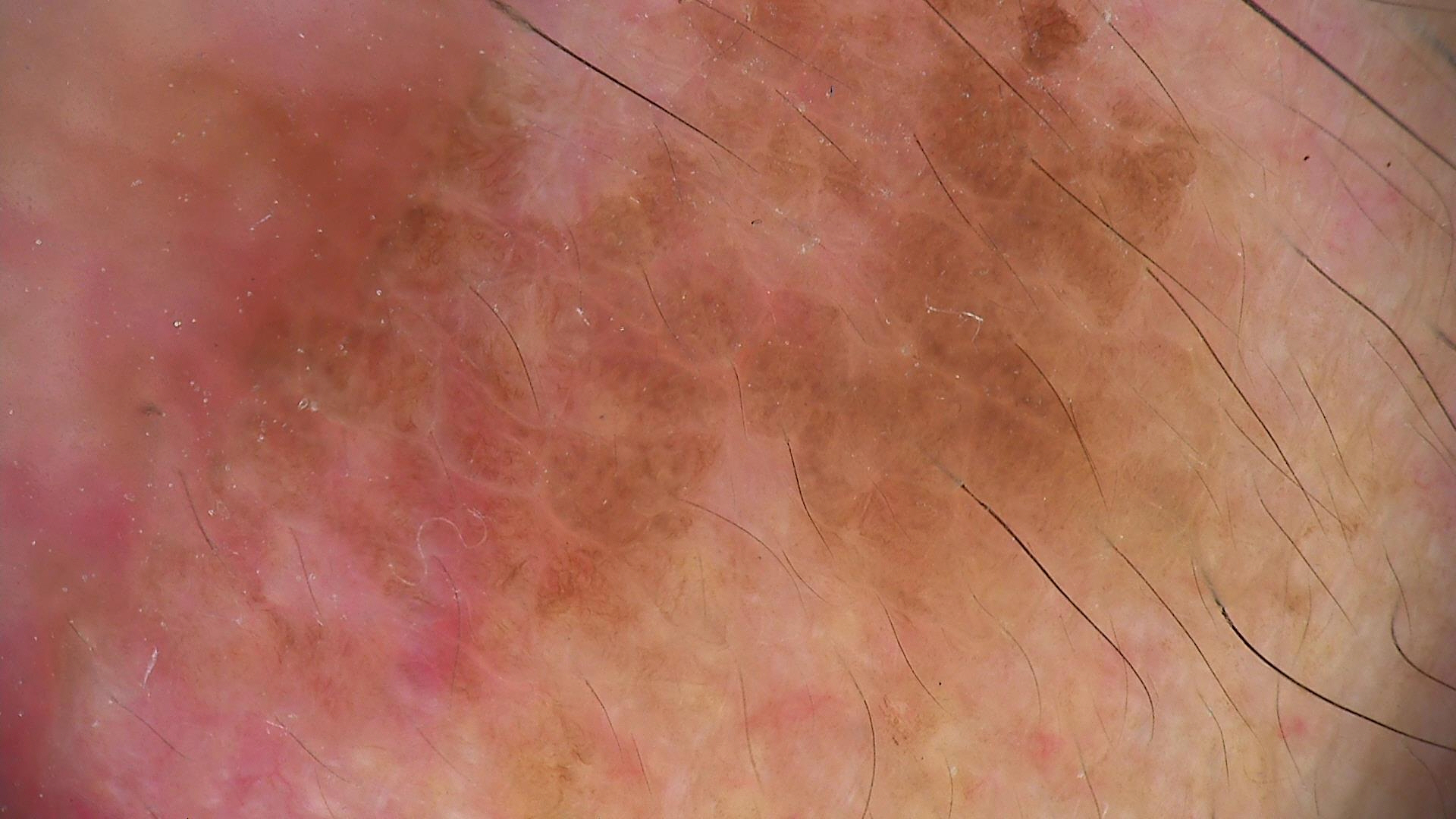The diagnosis was a seborrheic keratosis.